The photo was captured at an angle · the leg is involved · female subject, age 30–39 — 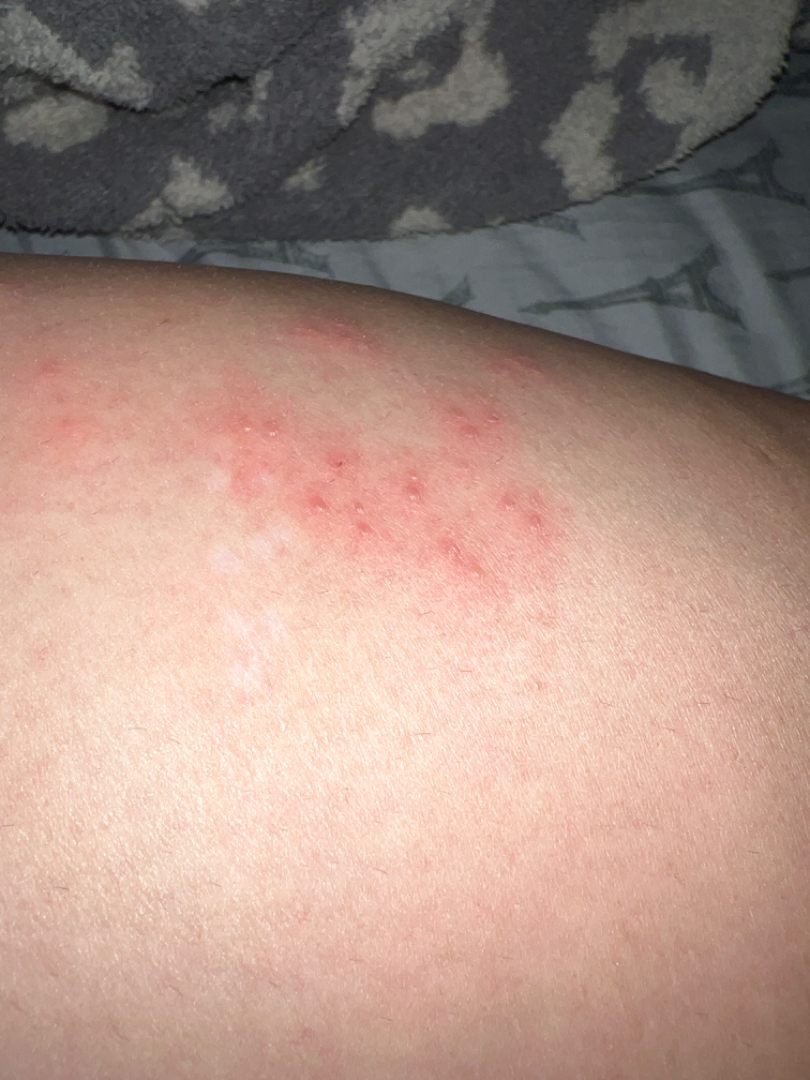{
  "texture": "fluid-filled",
  "differential": {
    "leading": [
      "Herpes Zoster"
    ],
    "unlikely": [
      "Insect Bite",
      "Molluscum Contagiosum",
      "Allergic Contact Dermatitis"
    ]
  }
}